Symptoms reported: itching · female patient, age 60–69 · reported duration is one to four weeks · the photograph is a close-up of the affected area · located on the arm: 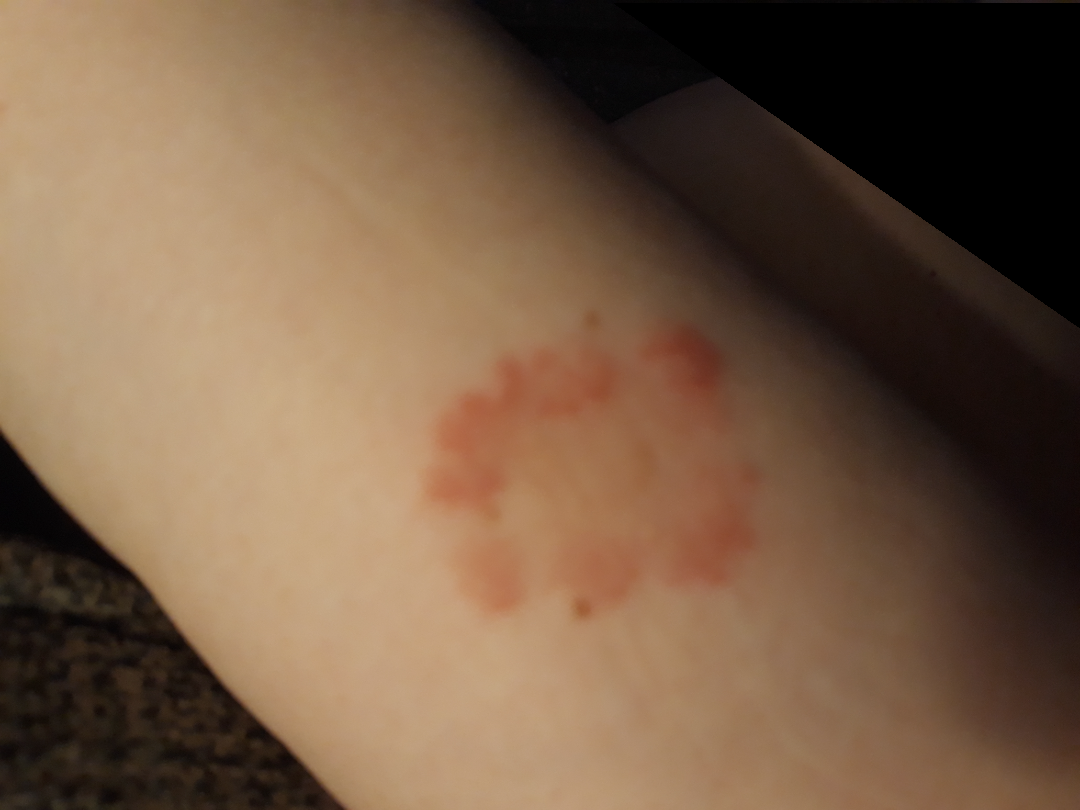Diagnostic features were not clearly distinguishable in this photograph.